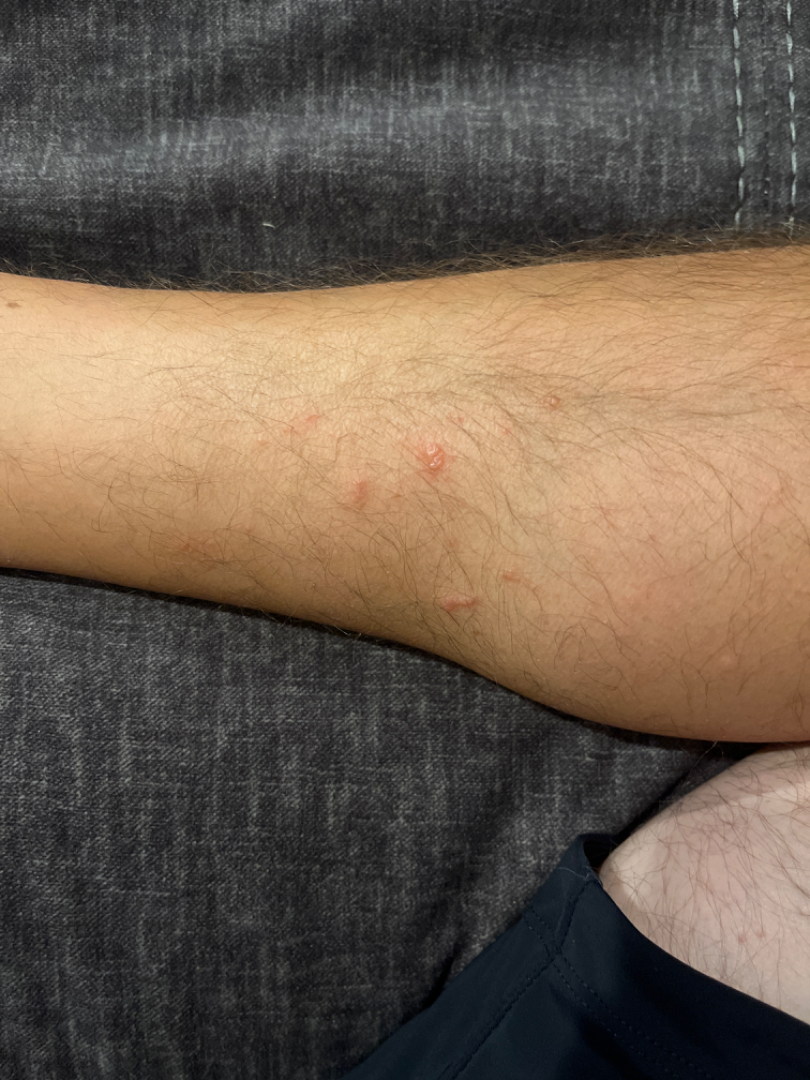Patient information:
No constitutional symptoms were reported. The affected area is the leg and arm. This image was taken at a distance. The patient is a male aged 18–29. Reported duration is one to four weeks. The contributor reports the lesion is fluid-filled and raised or bumpy. Self-categorized by the patient as a rash. Symptoms reported: enlargement and itching.
Review:
On remote dermatologist review: Contact dermatitis caused by Rhus diversiloba (leading).